A dermoscopic image of a skin lesion.
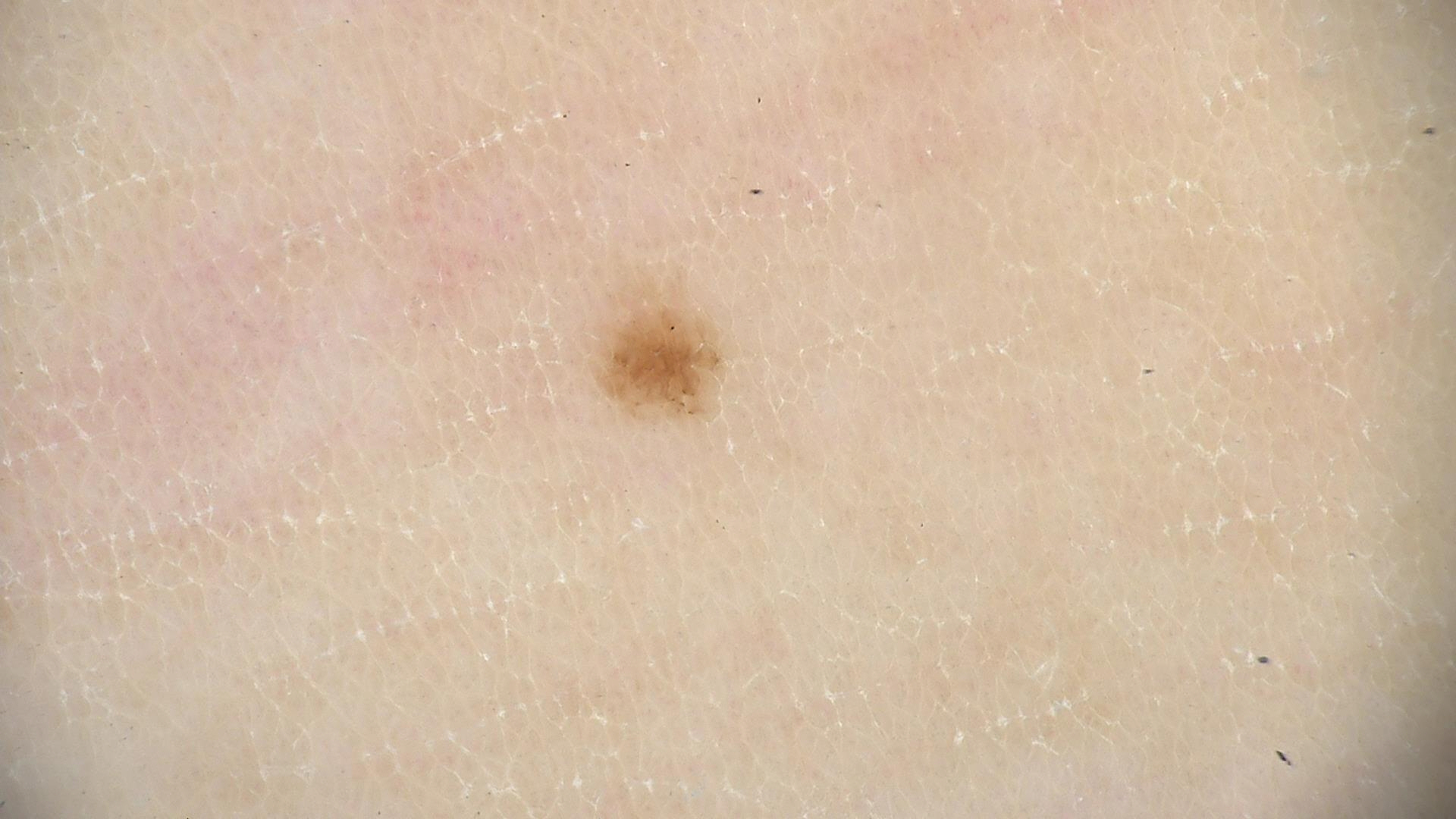diagnosis: dysplastic junctional nevus (expert consensus).